The patient is a male aged approximately 85 or older, a dermoscopic view of a skin lesion:
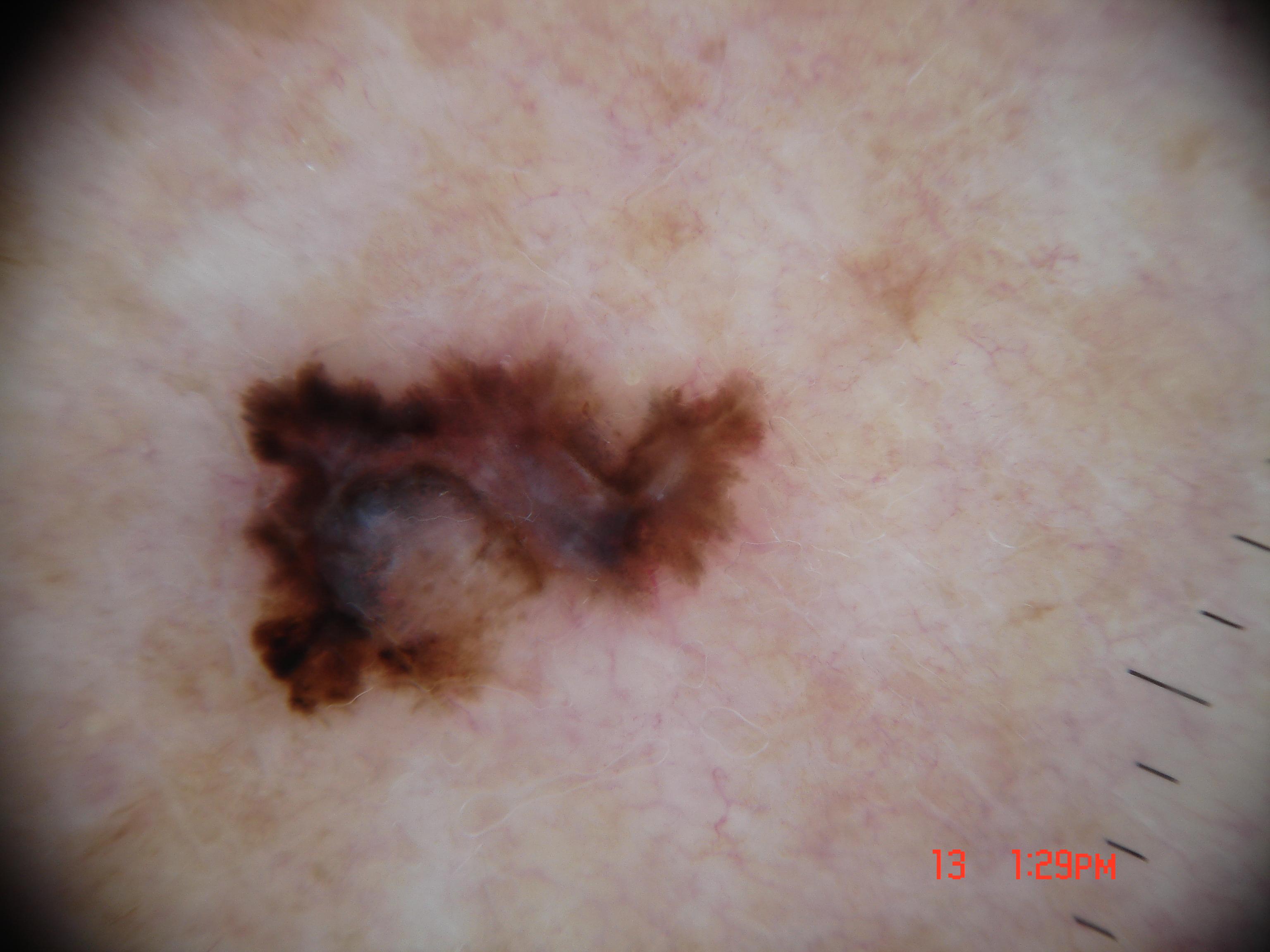The lesion takes up about 15% of the image.
The lesion is located at x1=224 y1=325 x2=787 y2=736.
Dermoscopically, the lesion shows streaks; no globules, pigment network, negative network, or milia-like cysts.
Confirmed on histopathology as a melanoma, a skin cancer.